A dermoscopy image of a single skin lesion.
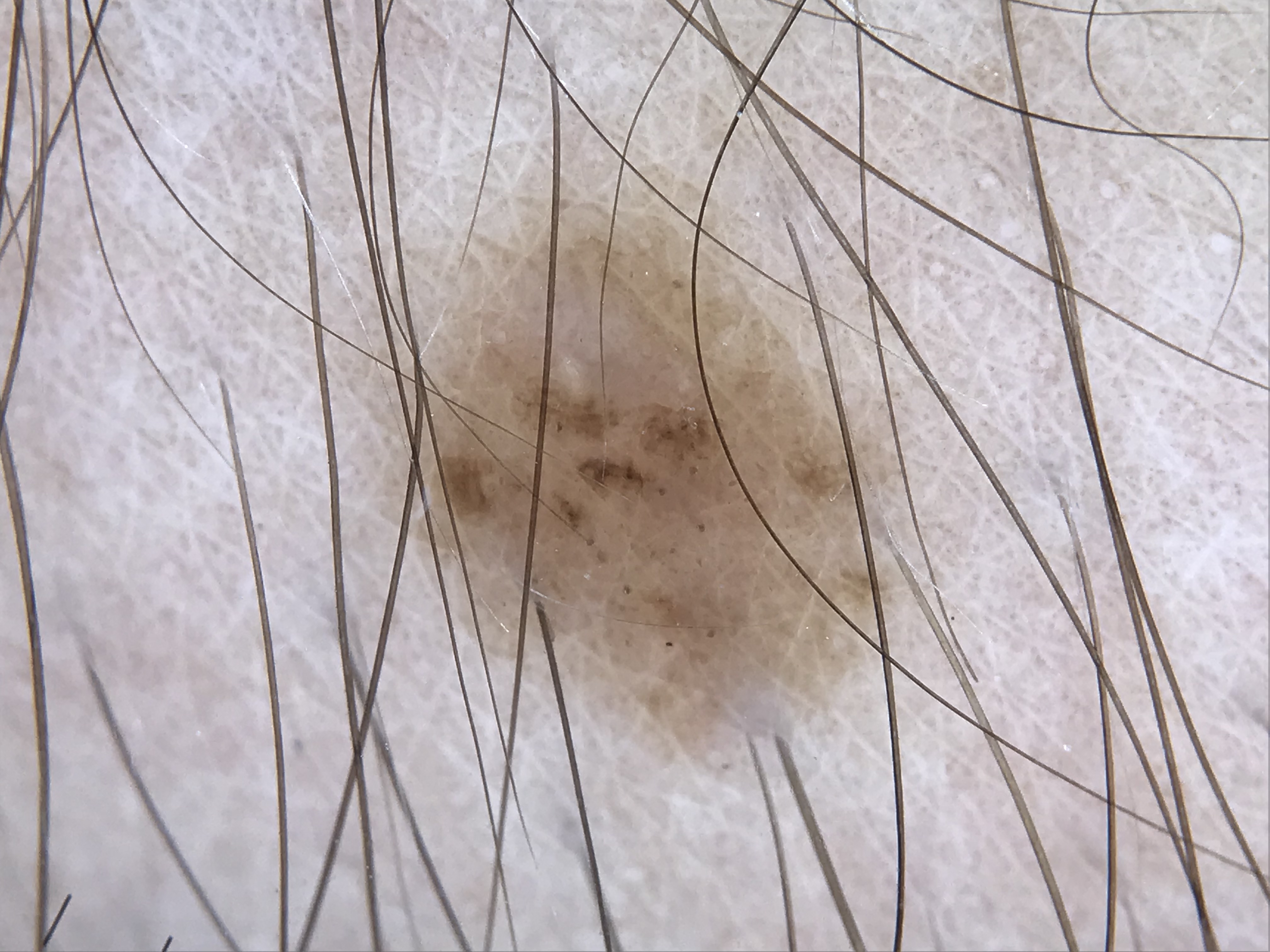The diagnosis was a dysplastic junctional nevus.